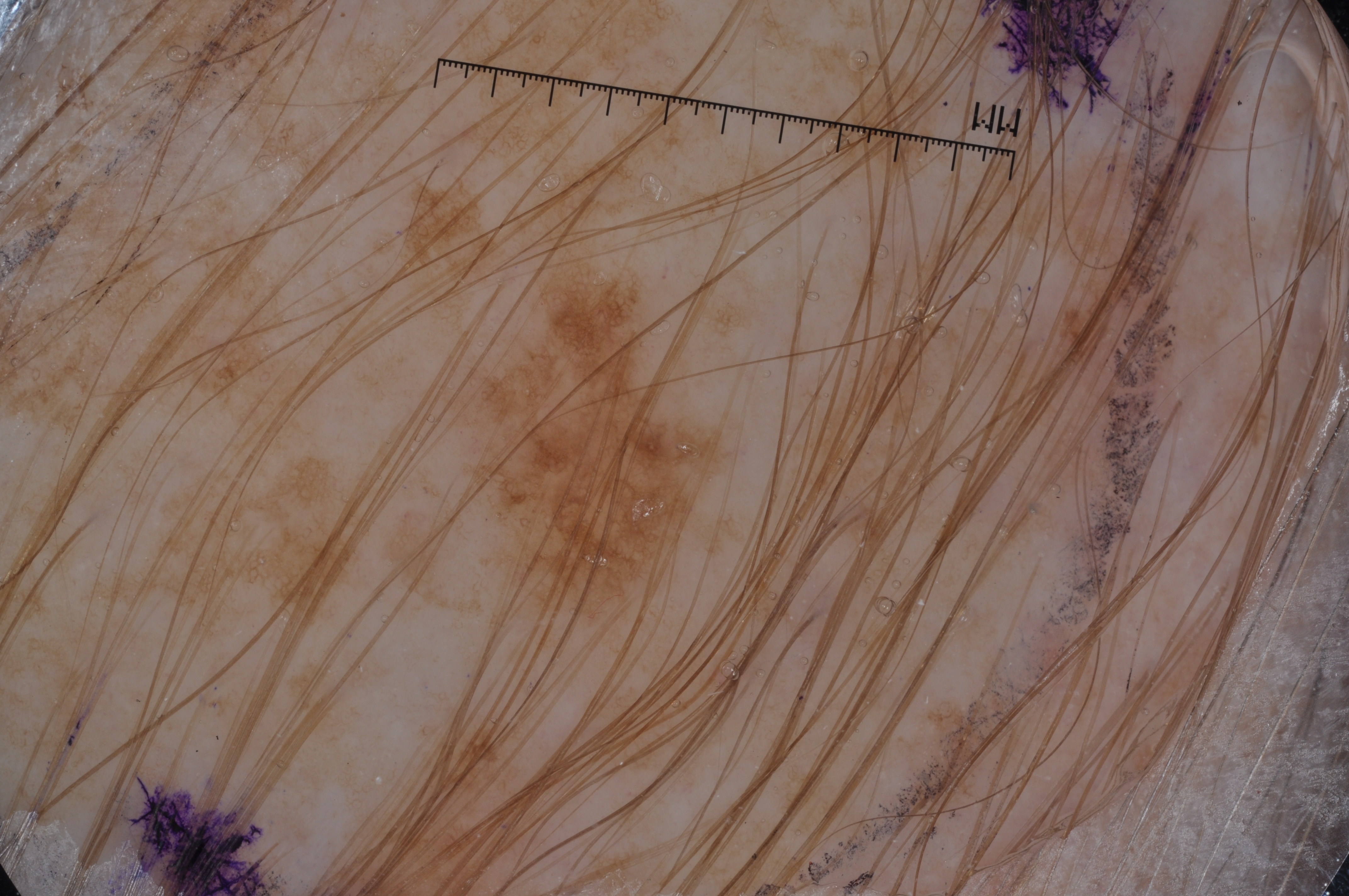The subject is a male aged 53-57.
A dermoscopic image of a skin lesion.
In (x1, y1, x2, y2) order, lesion location: bbox=[344, 165, 753, 649].
Dermoscopic review identifies pigment network; no milia-like cysts, streaks, or negative network.
Histopathological examination showed a melanoma, a malignancy.